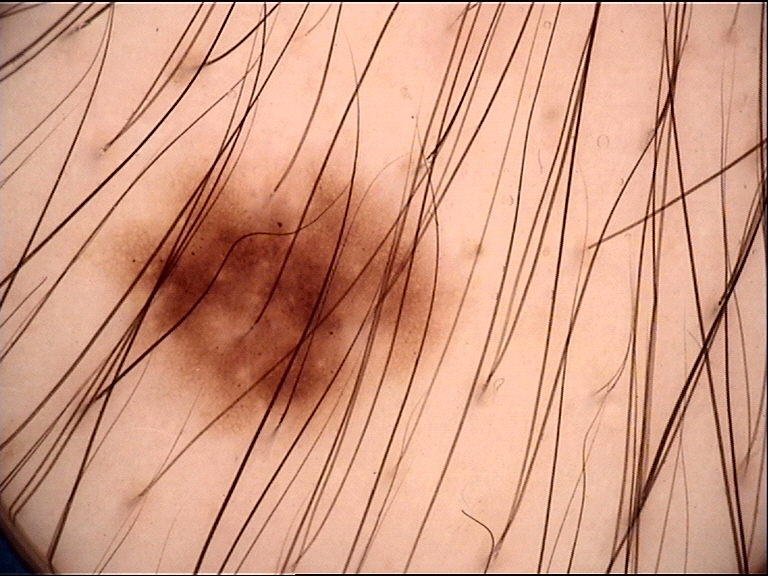The diagnosis was a dysplastic junctional nevus.